Dermoscopy of a skin lesion.
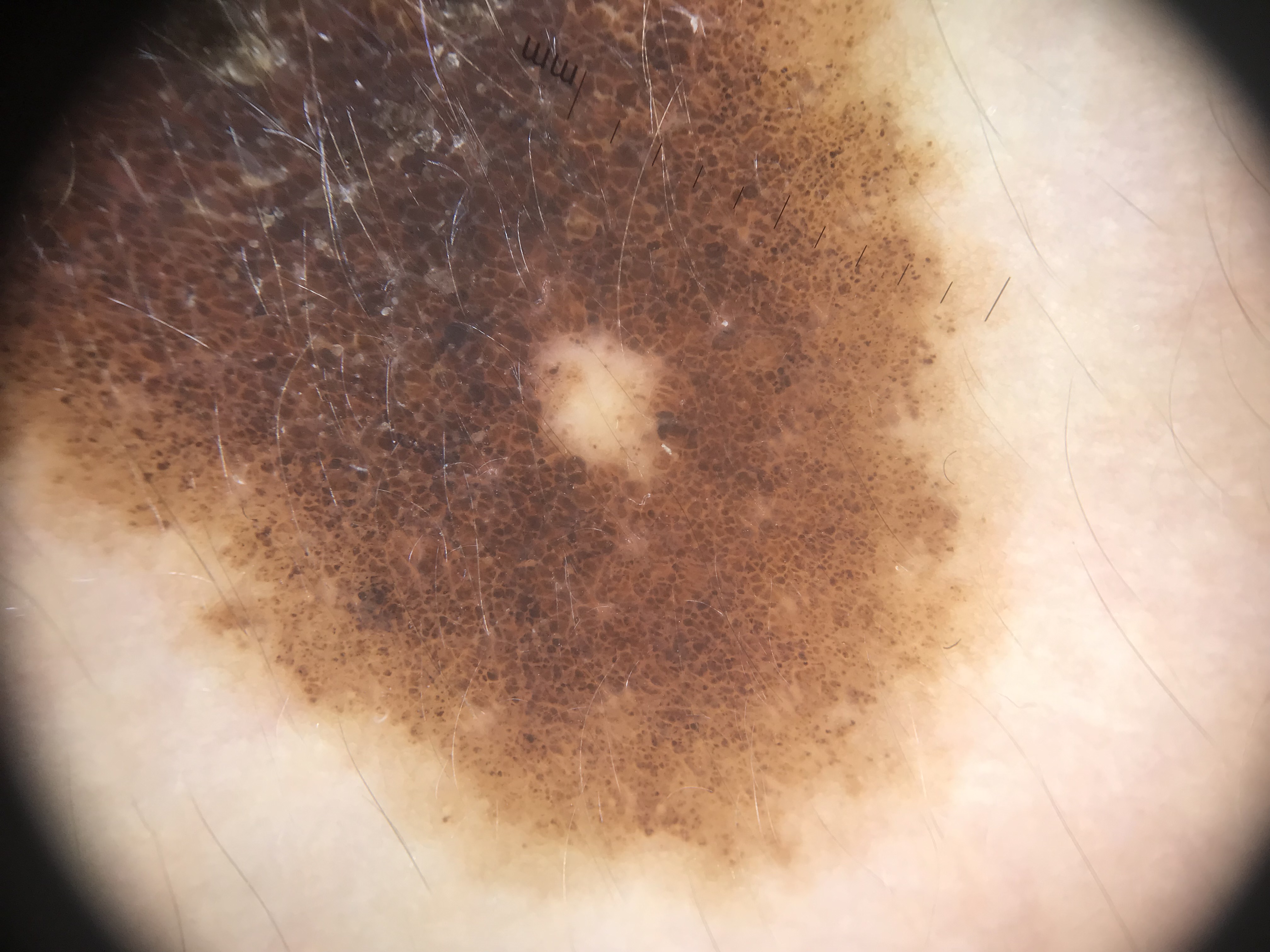The architecture is that of a banal lesion. Classified as a congenital compound nevus.